A skin lesion imaged with a dermatoscope — 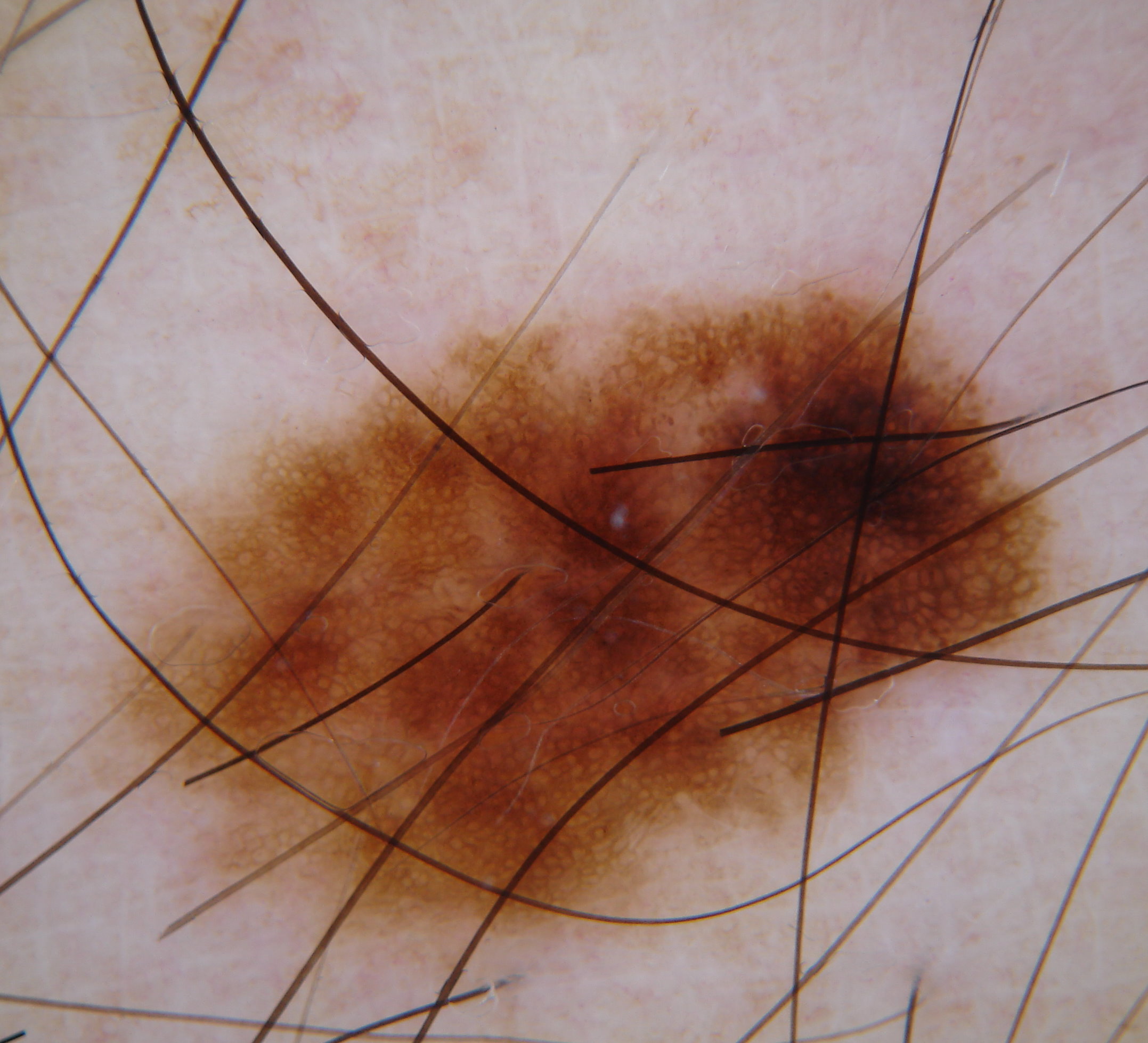<lesion>
  <dermoscopic_features>
    <present>globules, pigment network</present>
    <absent>negative network, streaks, milia-like cysts</absent>
  </dermoscopic_features>
  <lesion_location>
    <bbox_xyxy>78, 260, 1063, 991</bbox_xyxy>
  </lesion_location>
  <diagnosis>
    <name>melanocytic nevus</name>
    <malignancy>benign</malignancy>
    <lineage>melanocytic</lineage>
    <provenance>clinical</provenance>
  </diagnosis>
</lesion>